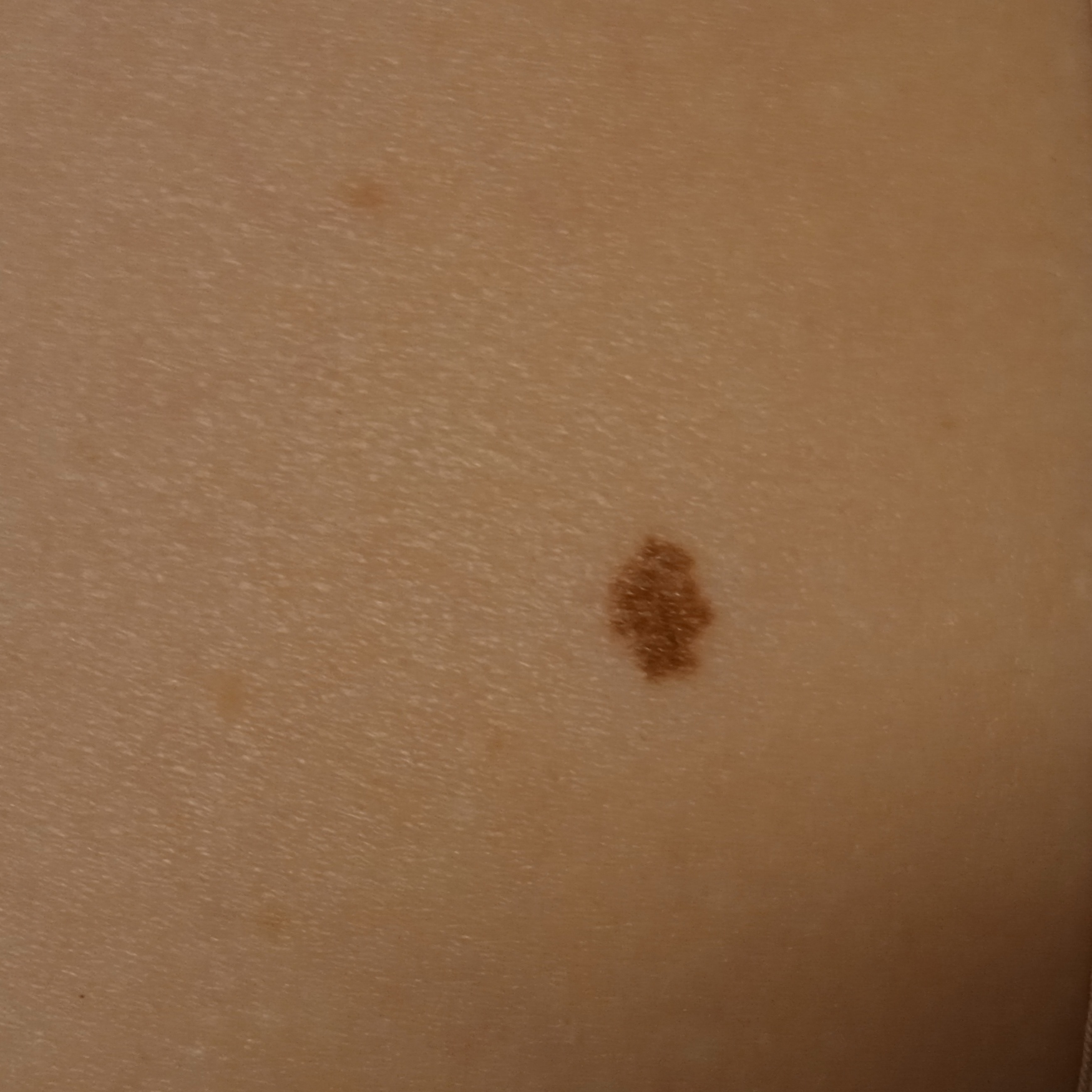By self-report, no sunbed use. A macroscopic clinical photograph of a skin lesion. The patient says their skin reddens with sun exposure. A female subject 27 years of age. Acquired for a research image collection, with no referral diagnosis. A moderate number of moles by the patient's own estimate. The lesion is located on an arm. Measuring roughly 6.4 mm. The diagnostic impression was an atypical (dysplastic) nevus.